An image taken at an angle: 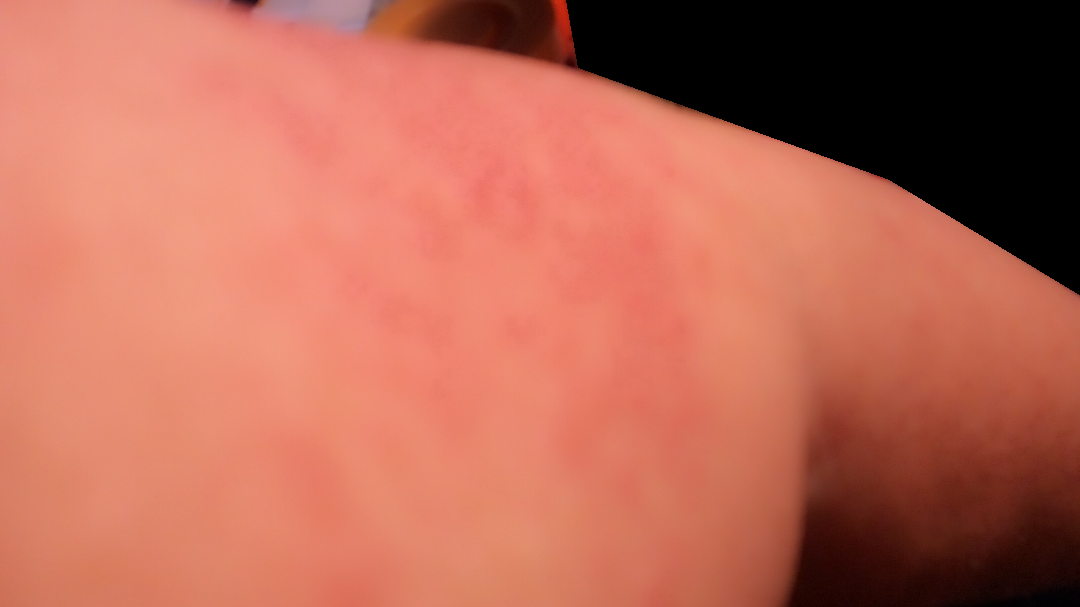No differential diagnosis could be assigned on photographic review.